A clinical photograph showing a skin lesion in context:
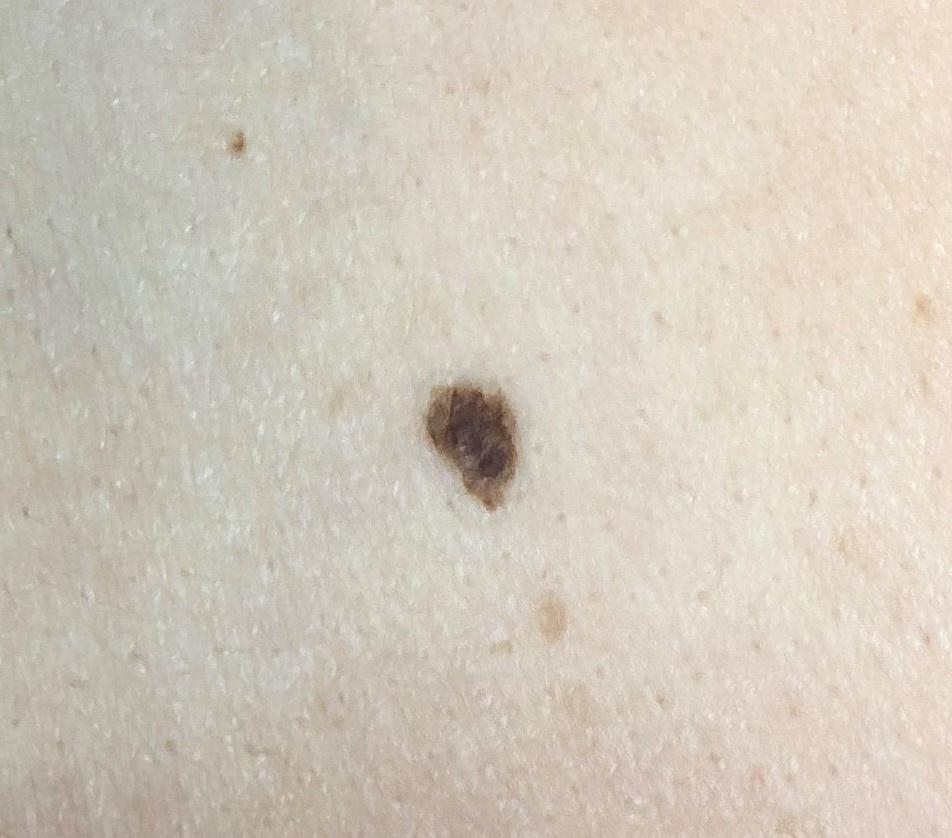{
  "diagnosis": {
    "name": "Nevus",
    "malignancy": "benign",
    "confirmation": "expert clinical impression",
    "lineage": "melanocytic"
  }
}